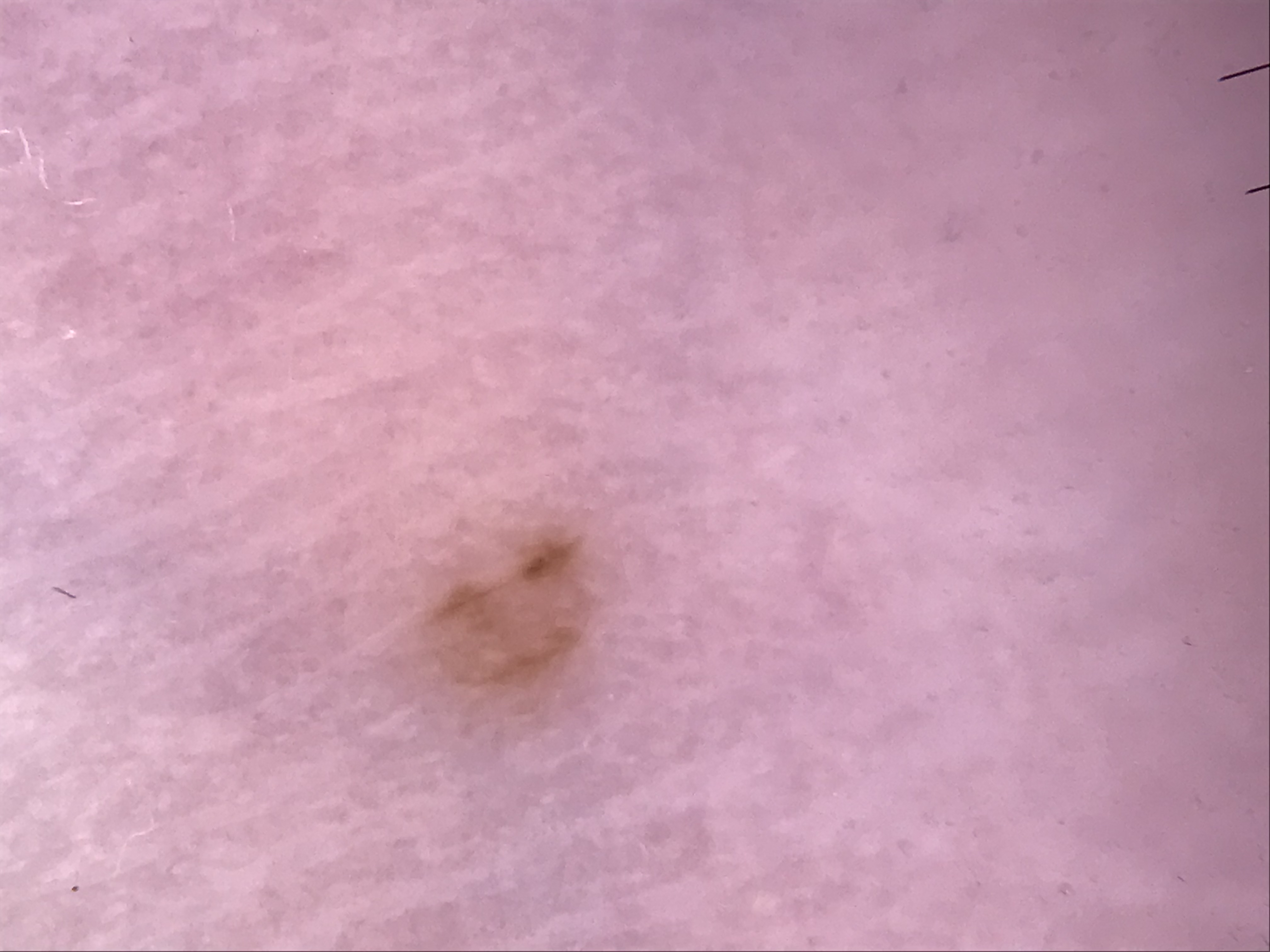Case: A skin lesion imaged with a dermatoscope. Impression: Consistent with an acral junctional nevus.